No relevant systemic symptoms, the back of the torso is involved, the photograph is a close-up of the affected area, the contributor notes itching, texture is reported as raised or bumpy — 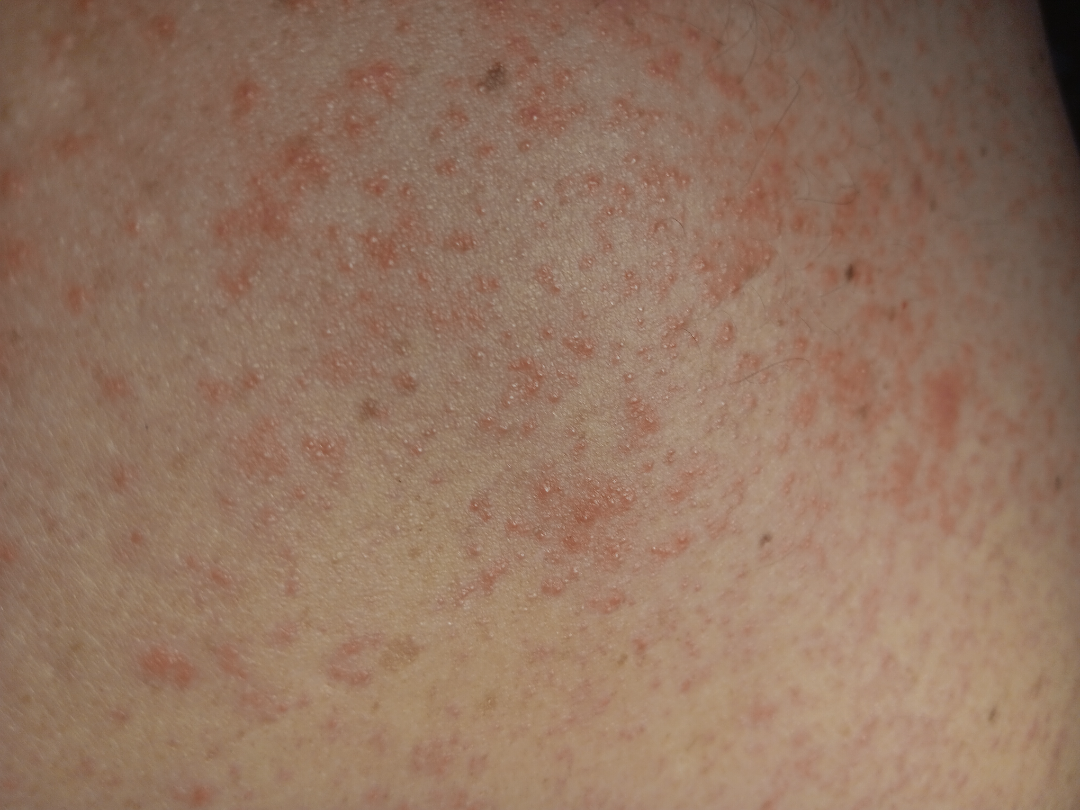Review: On remote dermatologist review: consistent with Acute dermatitis, NOS.